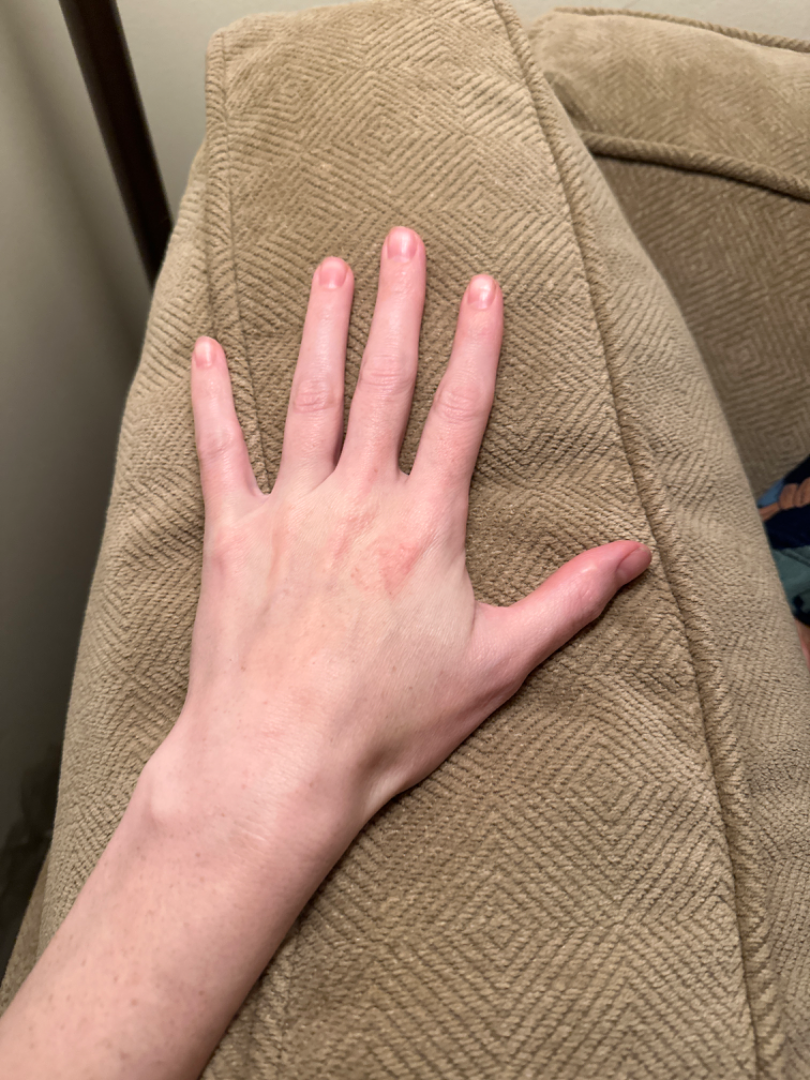• image framing: at a distance
• surface texture: raised or bumpy
• site: back of the hand
• patient-reported symptoms: bothersome appearance
• subject: female, age 30–39
• patient's own categorization: a rash
• skin tone: Fitzpatrick II; non-clinician graders estimated 2 on the MST
• other reported symptoms: joint pain and fatigue
• differential: most likely Granuloma annulare